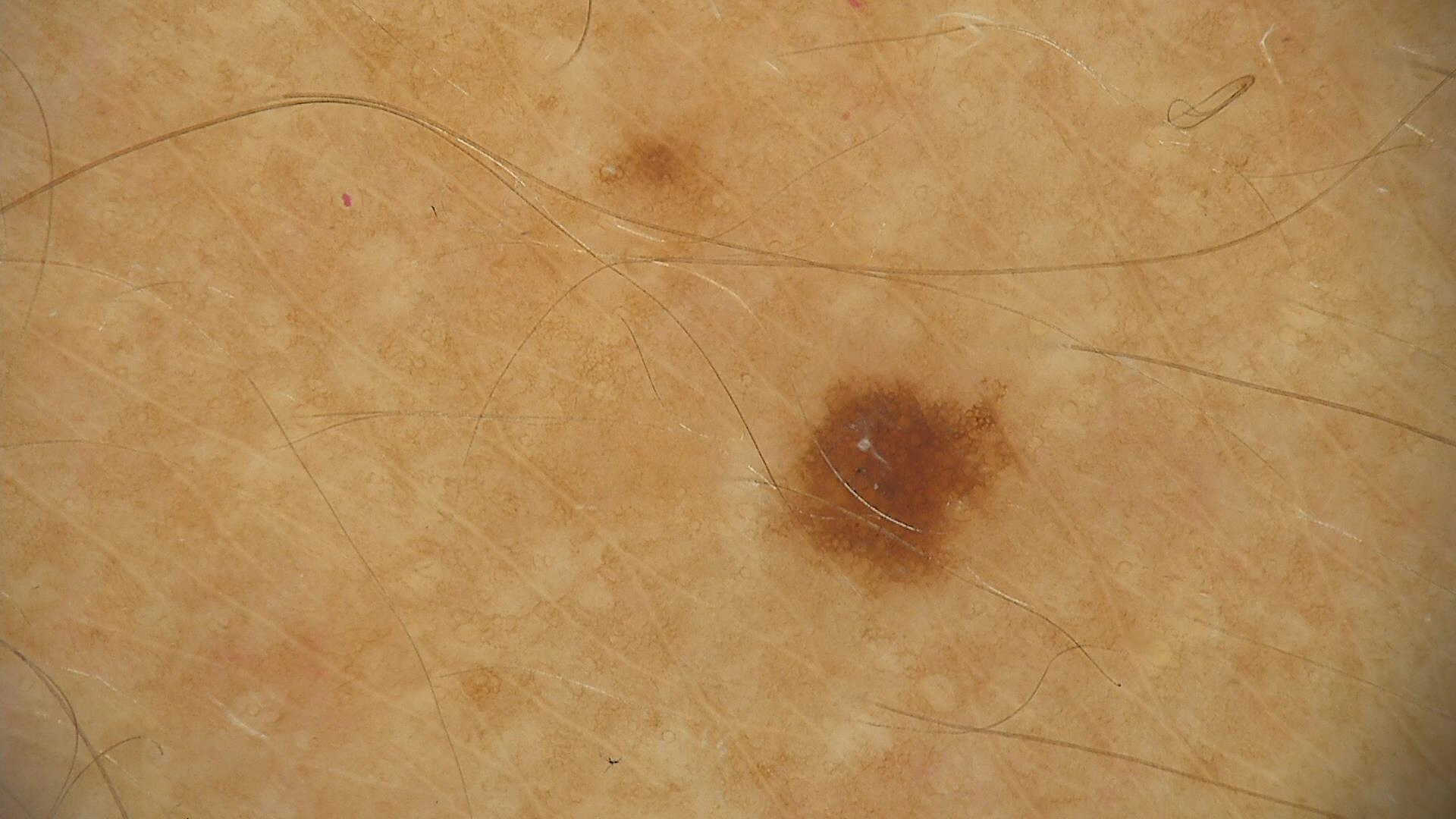{
  "diagnosis": {
    "name": "dysplastic junctional nevus",
    "code": "jd",
    "malignancy": "benign",
    "super_class": "melanocytic",
    "confirmation": "expert consensus"
  }
}